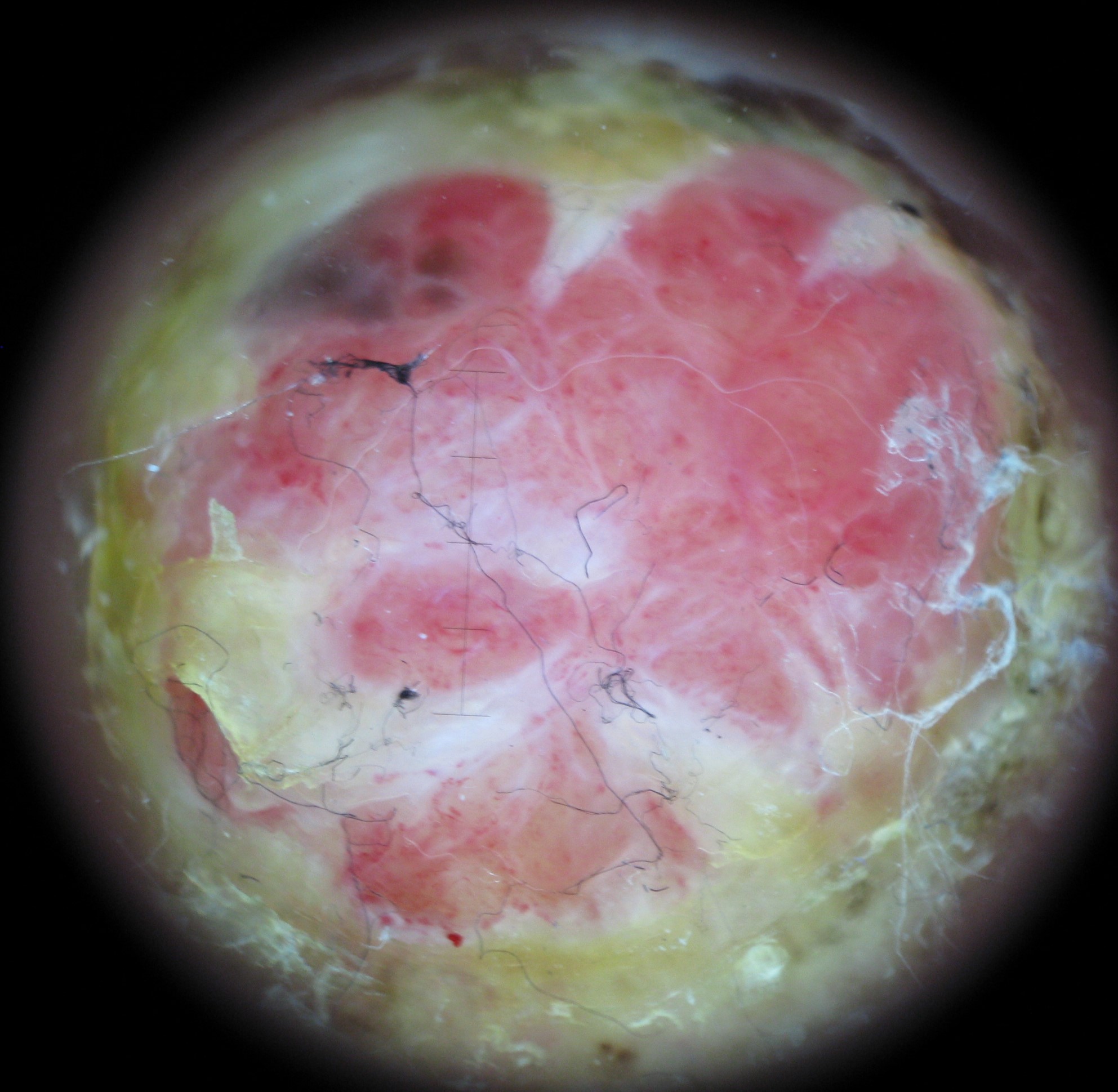pathology: acral nodular melanoma (biopsy-proven).